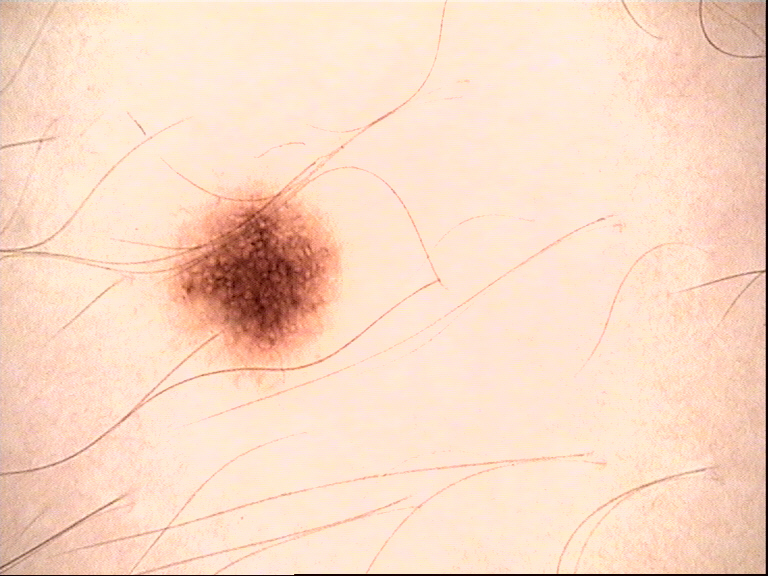Classified as a dysplastic junctional nevus.